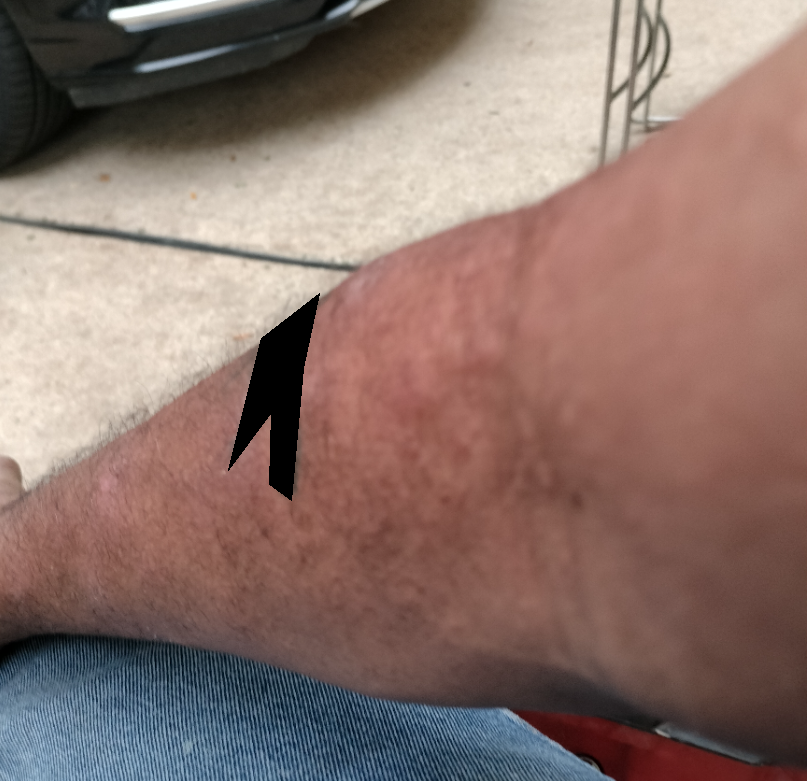The affected area is the arm.
The contributor is male.
The photograph was taken at an angle.
On dermatologist assessment of the image: Eczema (primary).